A dermoscopic image of a skin lesion. Imaged for a research study, with no referral diagnosis recorded. The patient says their skin tans without first burning. By self-report, a personal history of cancer, a personal history of skin cancer, no immunosuppression, and no sunbed use:
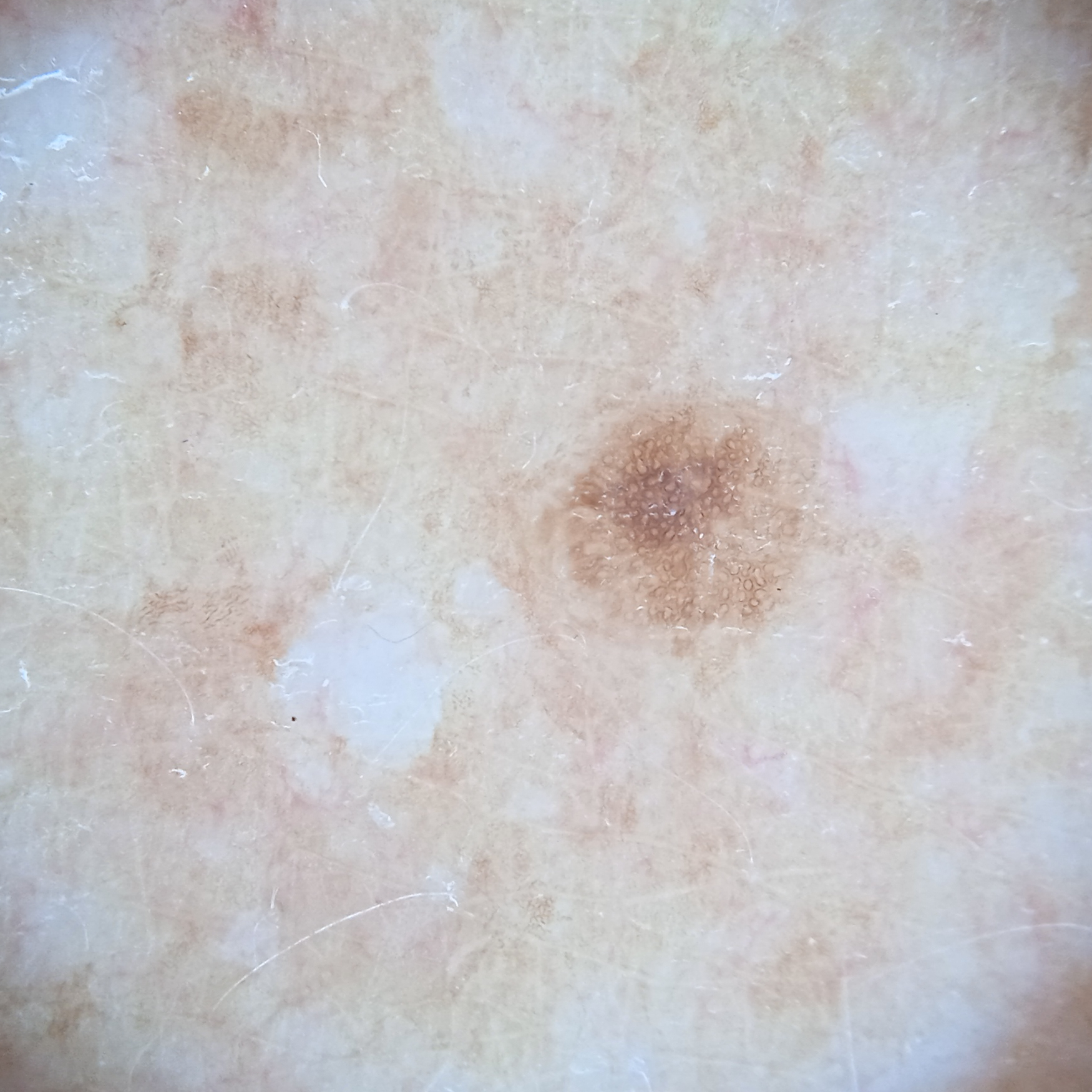| feature | finding |
|---|---|
| location | the back |
| lesion size | 2.7 mm |
| assessment | melanocytic nevus (dermatologist consensus) |